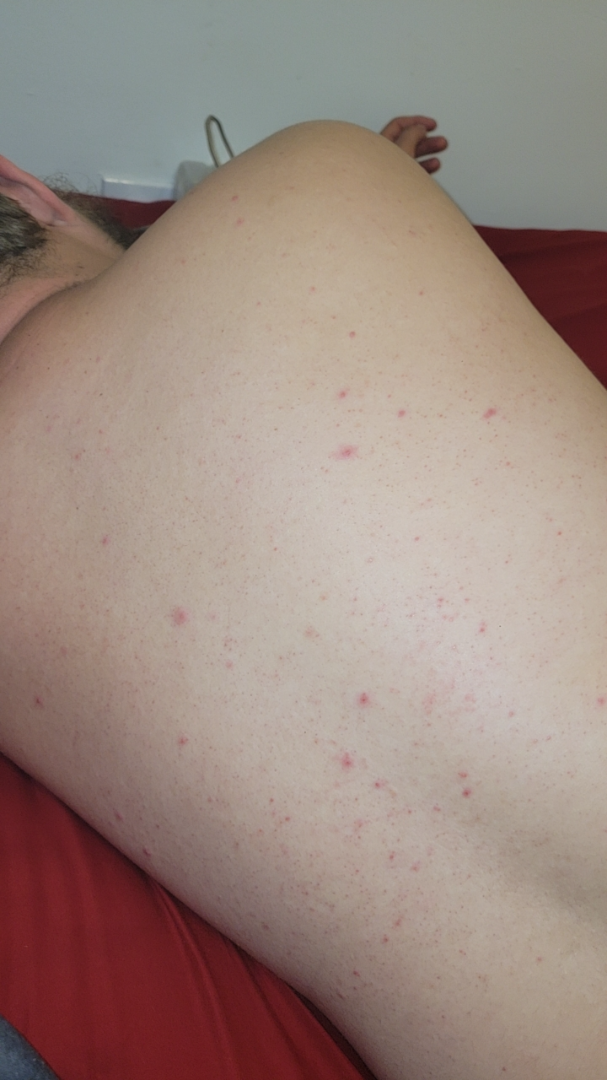The reviewing clinician's impression was: most consistent with Folliculitis; an alternative is Acne.